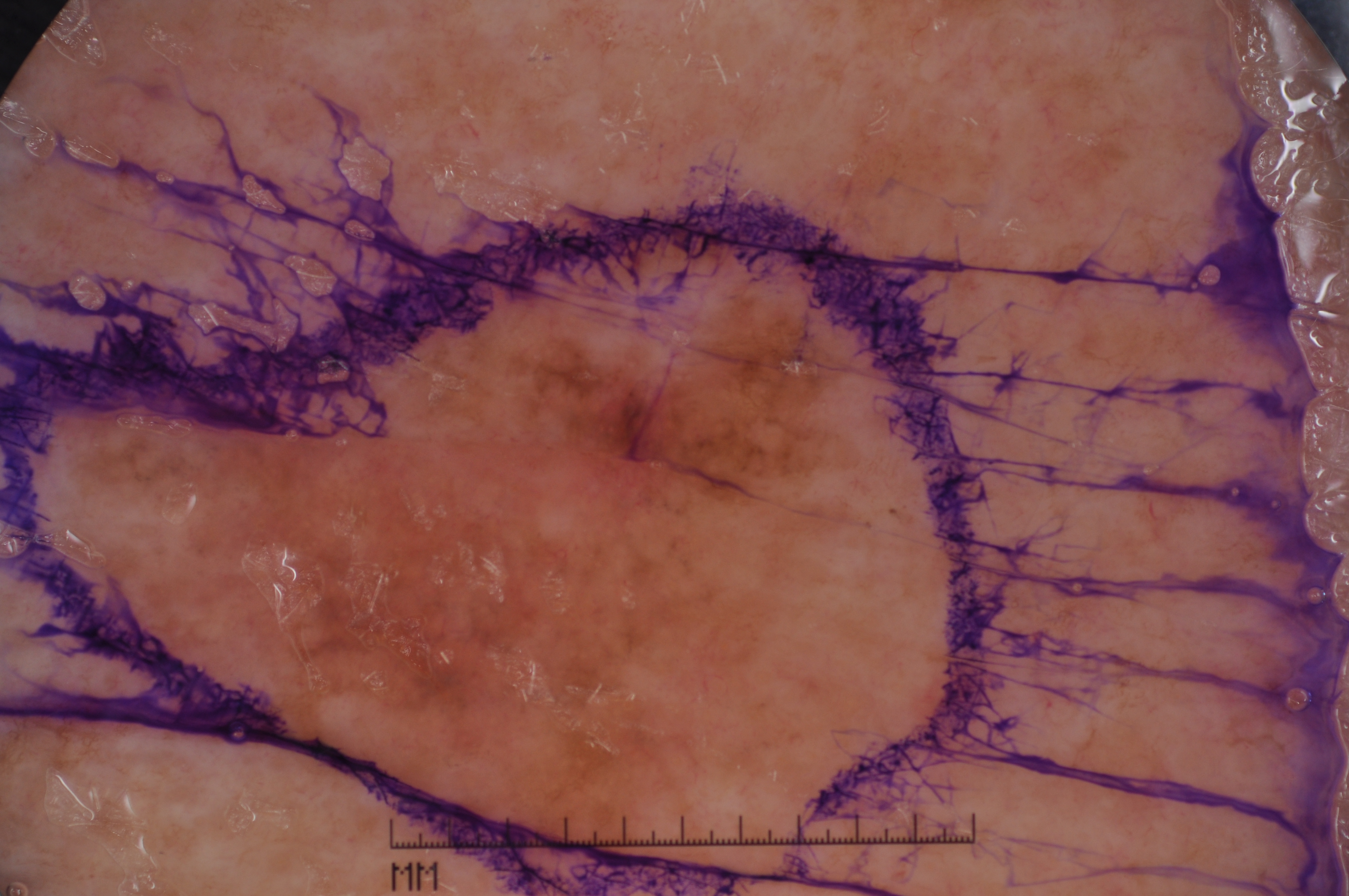Case summary:
A dermoscopic close-up of a skin lesion. The lesion is bounded by x1=33 y1=210 x2=949 y2=875. The lesion occupies roughly 35% of the field. Dermoscopic assessment notes pigment network; no negative network, milia-like cysts, or streaks.
Conclusion:
Histopathological examination showed a melanoma, a skin cancer.